A dermoscopic close-up of a skin lesion.
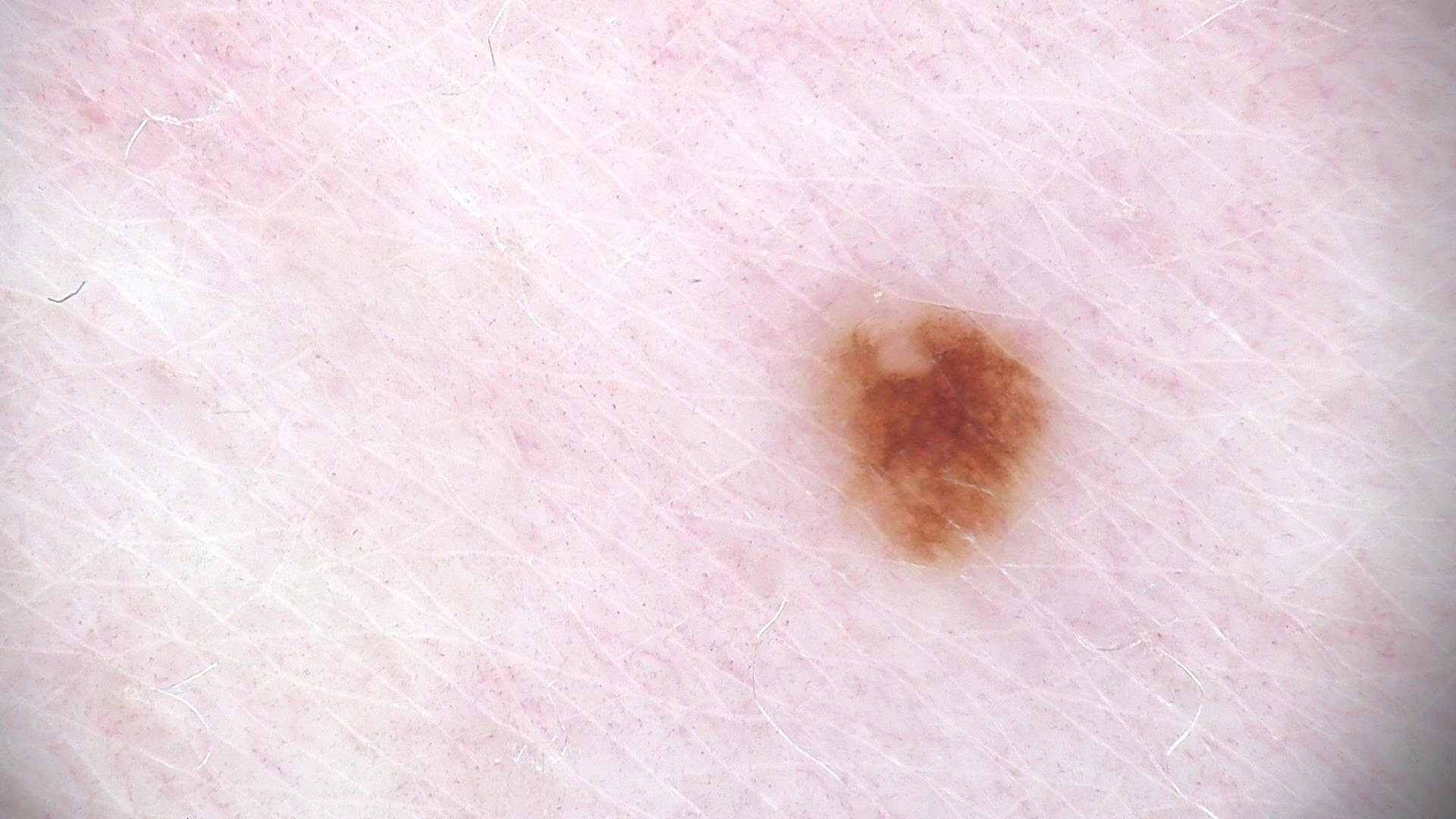assessment = dysplastic junctional nevus (expert consensus).